Recorded as Fitzpatrick phototype III; a skin lesion imaged with a dermatoscope; a male patient aged 38 to 42; the chart notes melanoma in a first-degree relative.
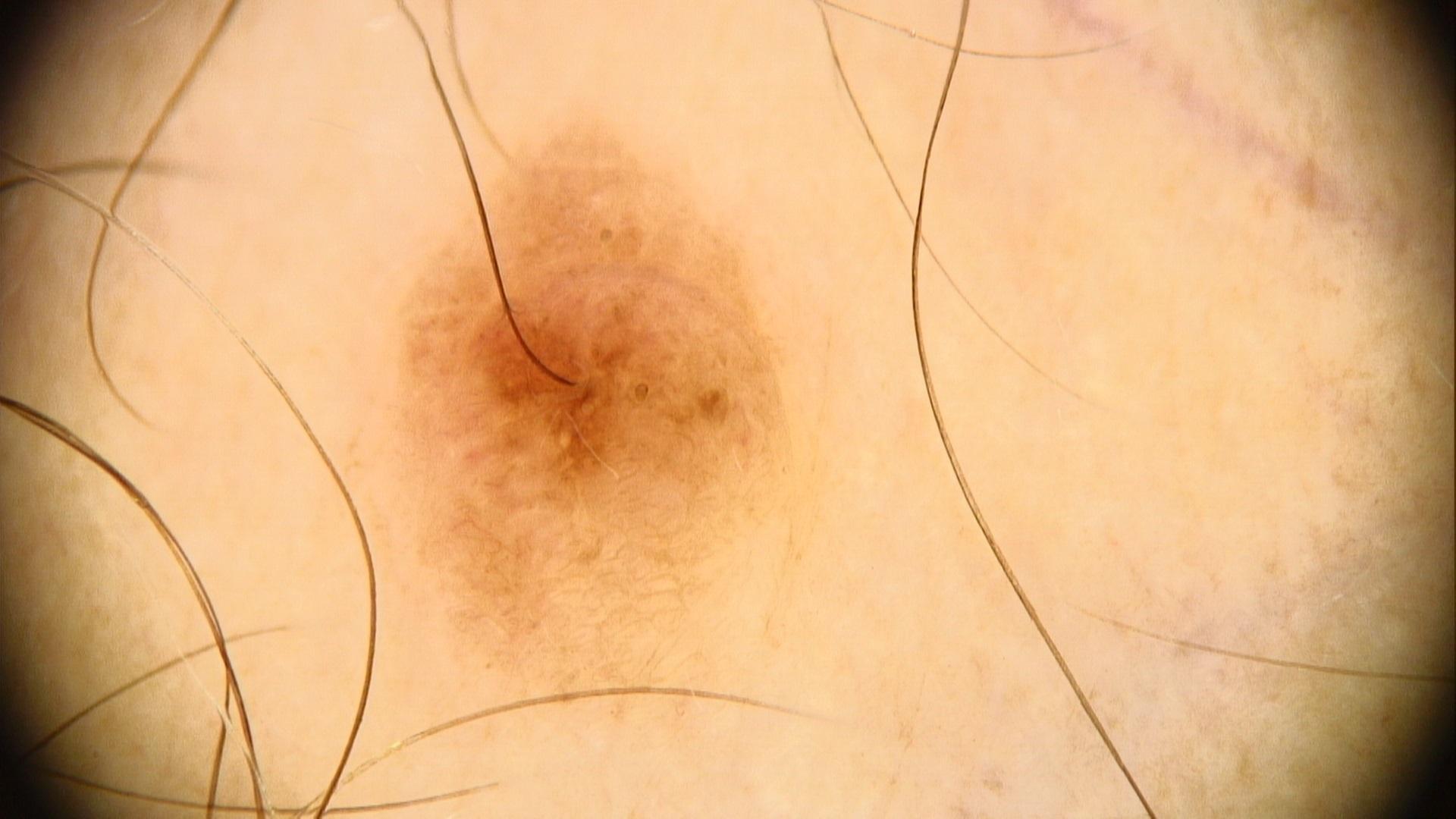Case summary:
The lesion involves a lower extremity.
Impression:
The clinical assessment was a lesion of melanocytic origin — a nevus.